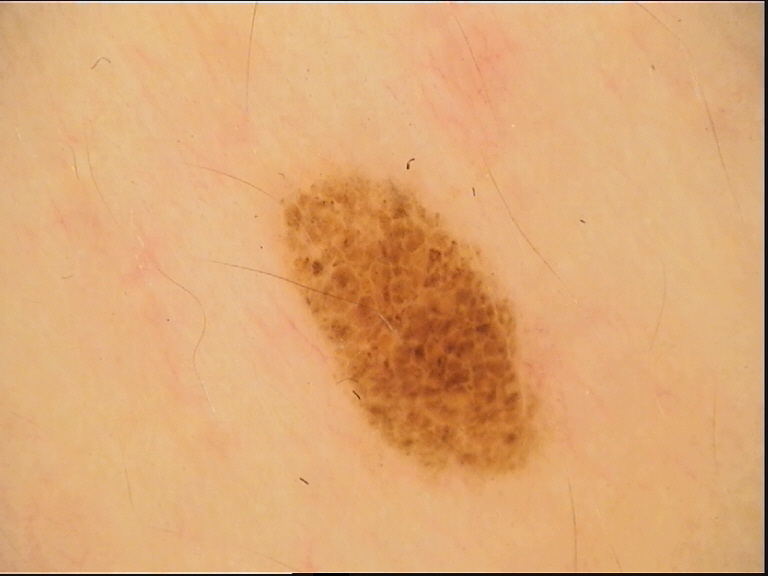The diagnosis was a dysplastic compound nevus.